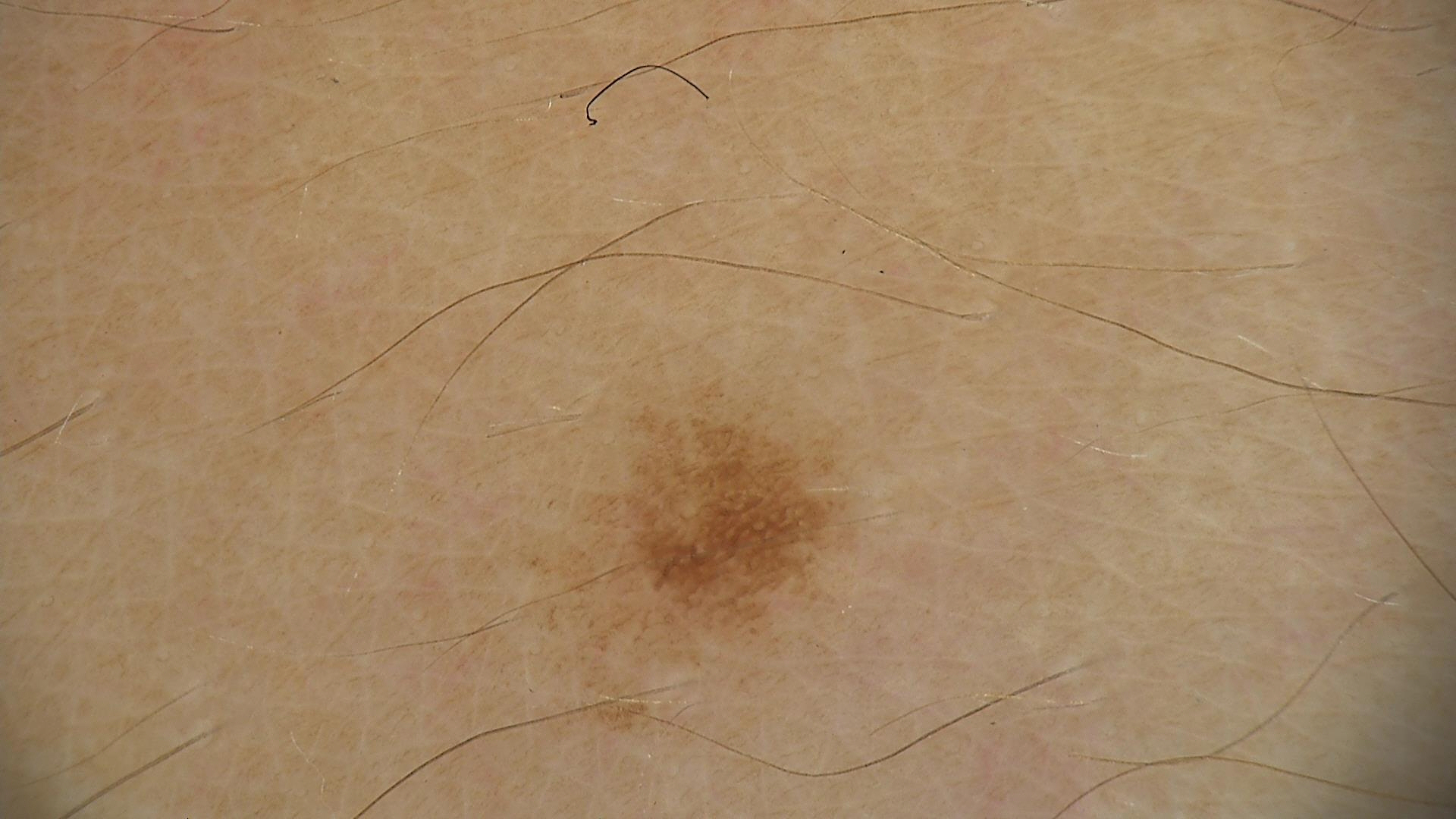A dermatoscopic image of a skin lesion. The diagnosis was a dysplastic junctional nevus.